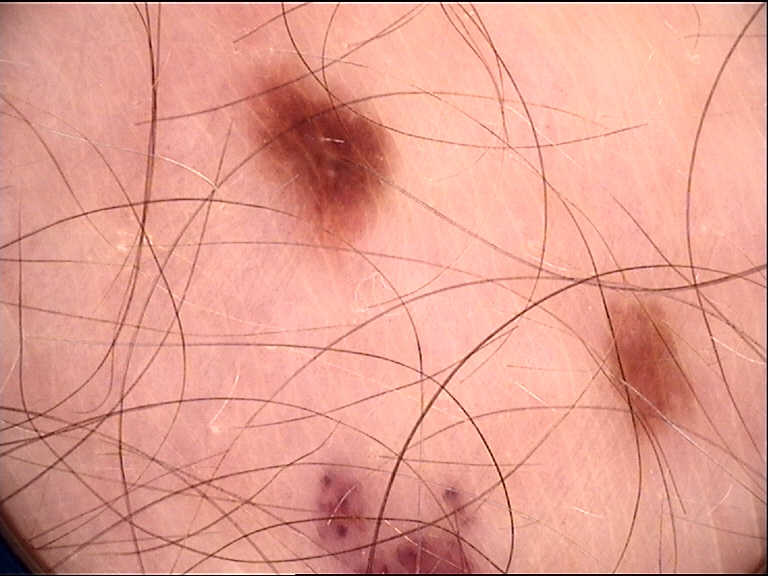Impression:
Labeled as a dysplastic junctional nevus.